A dermoscopy image of a skin lesion. Referred with a clinical suspicion of basal cell carcinoma:
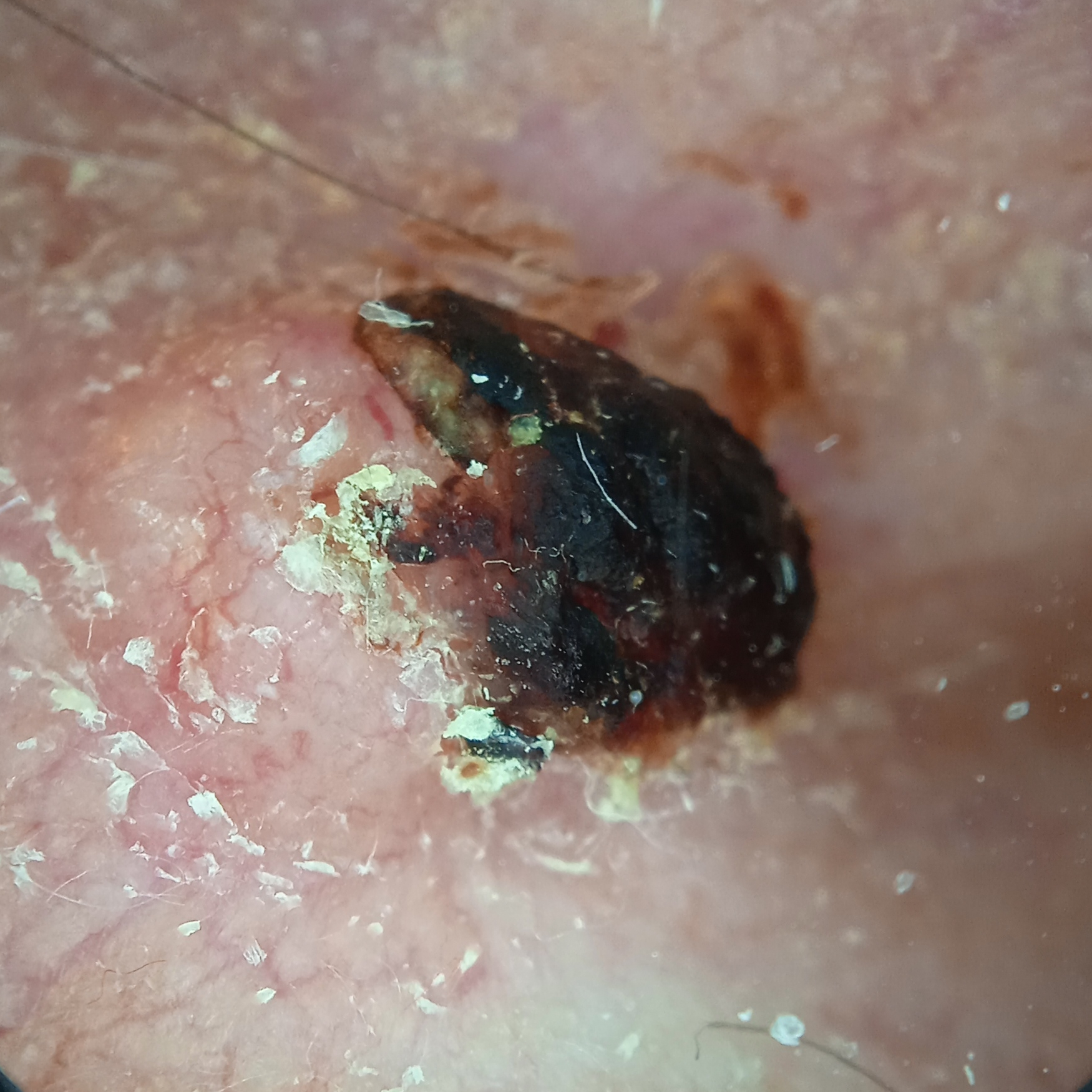{
  "lesion_location": "the head",
  "diagnosis": {
    "name": "basal cell carcinoma",
    "malignancy": "malignant",
    "procedure": "excision",
    "tumor_thickness_mm": 2.7
  }
}